A patient age 67 · a clinical photo of a skin lesion taken with a smartphone — 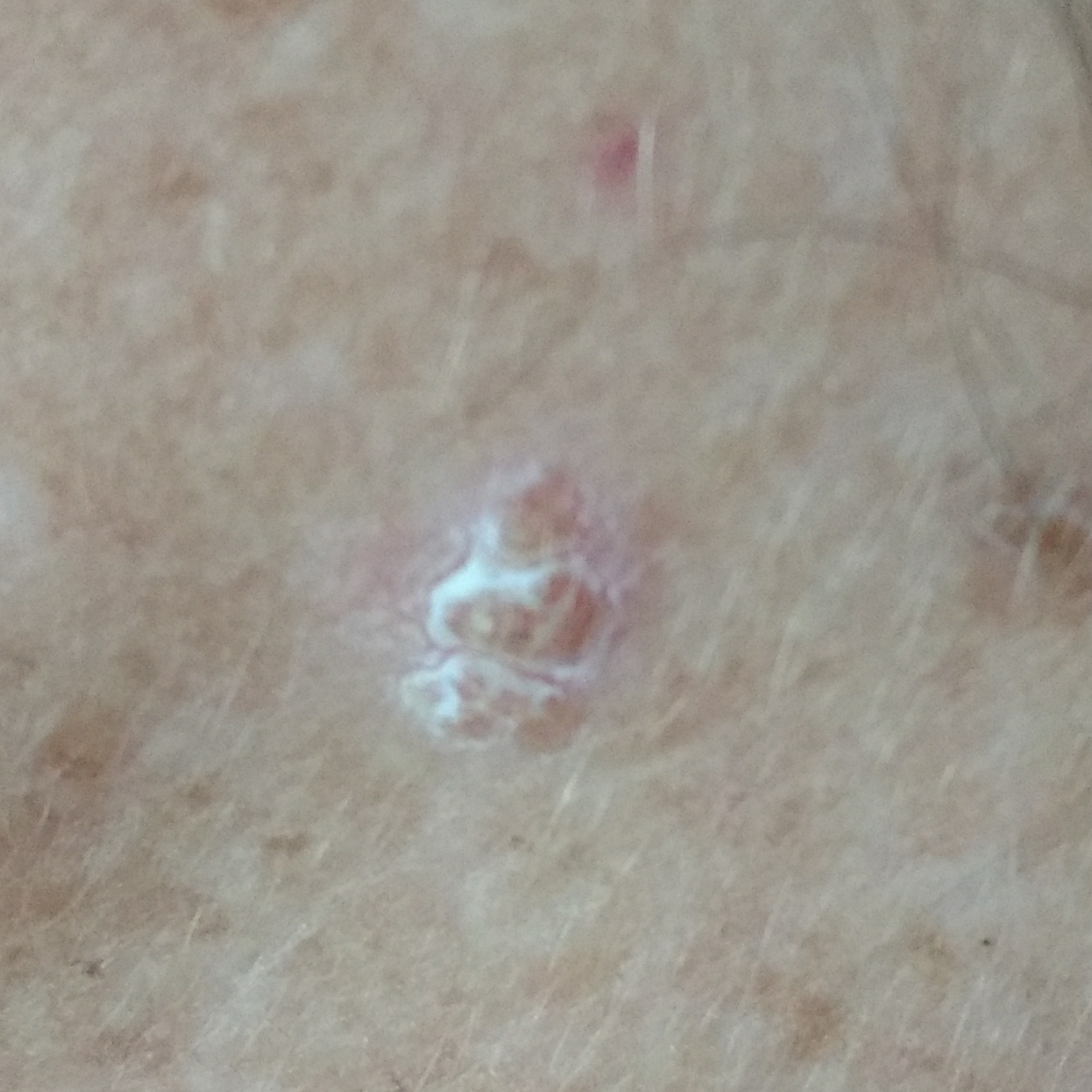location: the face
patient-reported symptoms: itching, elevation / no growth
assessment: actinic keratosis (clinical consensus)